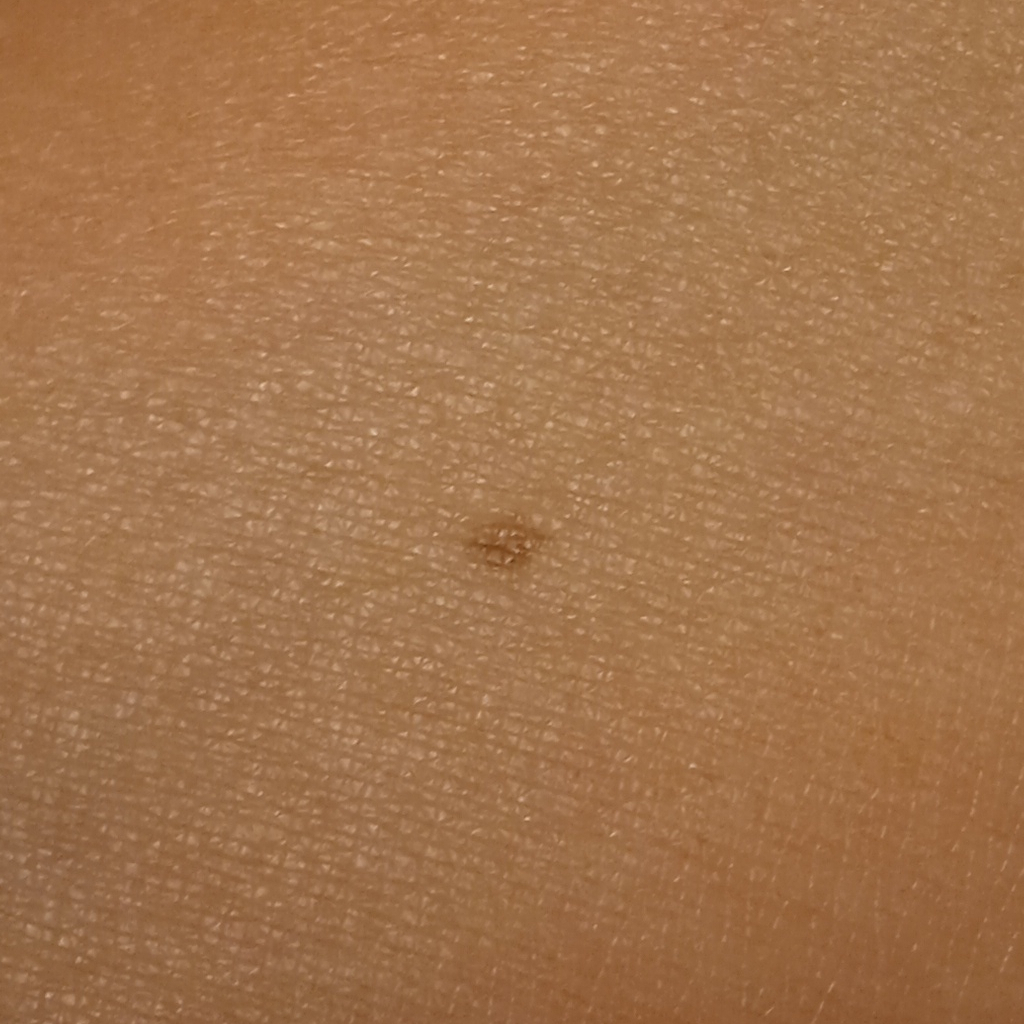Case:
- sun reaction — skin tans without first burning
- risk factors — a history of sunbed use
- patient — female, 47 years old
- referral context — research study (no referral diagnosis)
- imaging — clinical photo
- nevus count — a moderate number of melanocytic nevi
- site — an arm
- diameter — 2.7 mm
- diagnostic label — melanocytic nevus (dermatologist consensus)